An image taken at a distance · located on the arm · the subject is male · the patient considered this a rash · reported duration is one to four weeks · skin tone: Fitzpatrick II; non-clinician graders estimated a Monk skin tone scale of 3 · symptoms reported: bothersome appearance and itching · texture is reported as raised or bumpy:
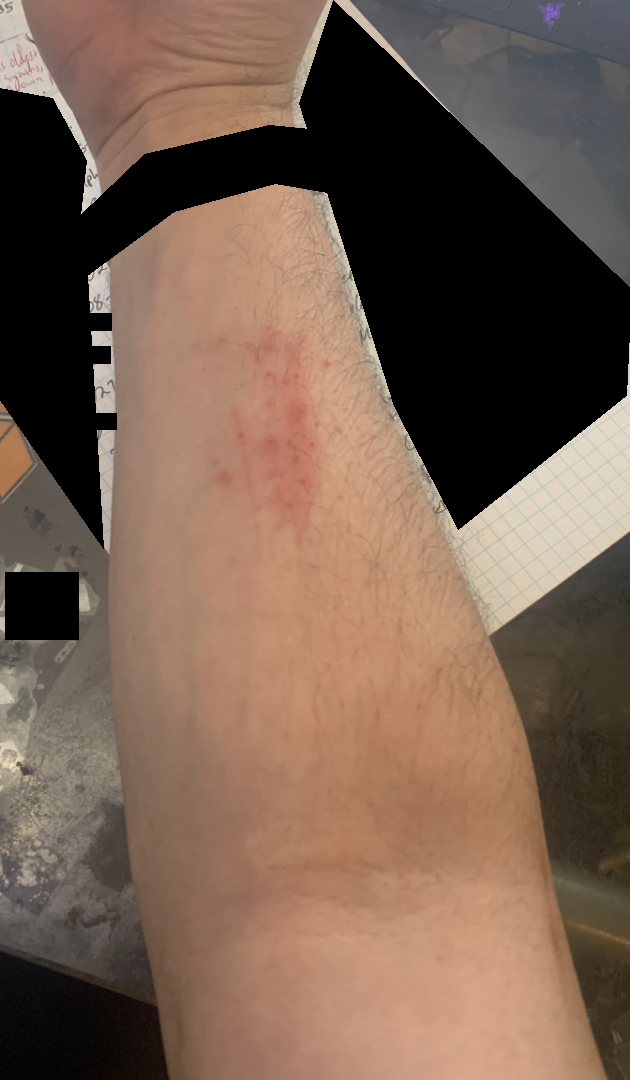Findings: On remote dermatologist review: most likely Superficial wound of body region; also raised was Skin and soft tissue atypical mycobacterial infection; possibly SCC/SCCIS.